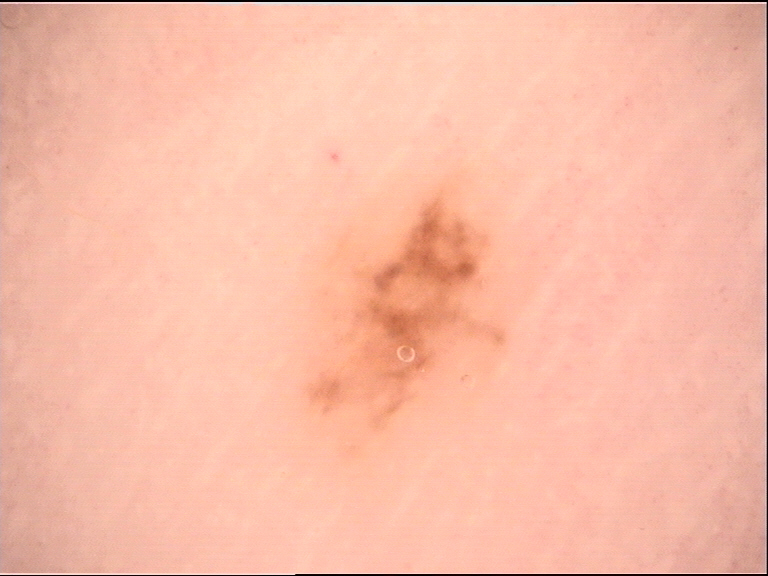assessment: acral junctional nevus (expert consensus).